The photograph was taken at an angle. The arm is involved. The subject is 18–29, female — 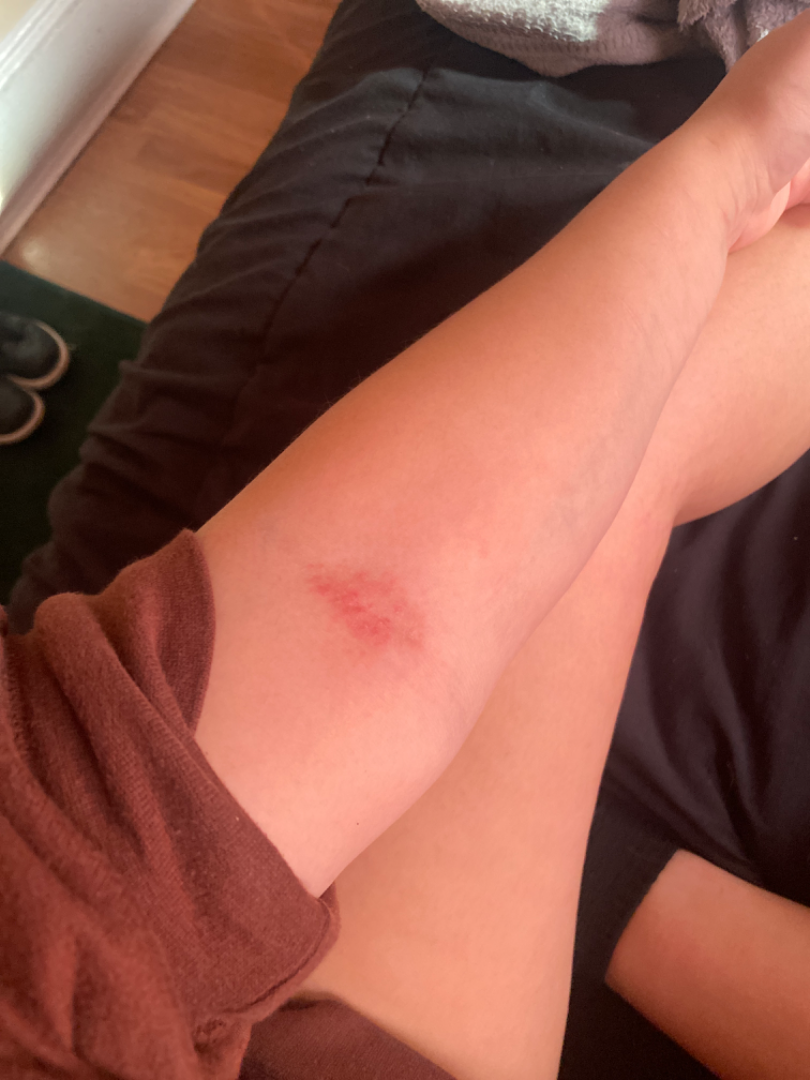  systemic_symptoms: none reported
  patient_category: a rash
  symptoms:
    - pain
    - burning
    - itching
  skin_tone:
    fitzpatrick: I
  duration: one to three months
  texture: rough or flaky
  differential:
    leading:
      - Allergic Contact Dermatitis
    considered:
      - Abrasion, scrape, or scab
      - Eczema